A dermoscopic photograph of a skin lesion.
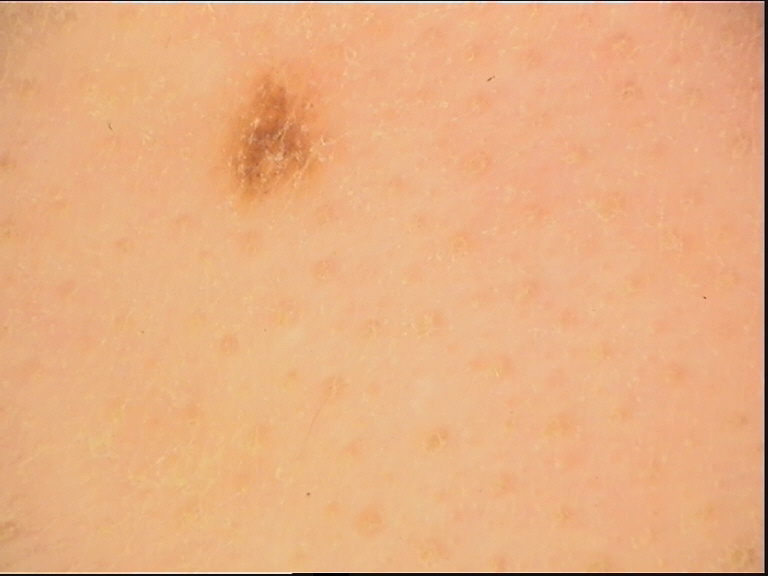This is a banal lesion. Classified as a junctional nevus.